Acquired for a research image collection, with no referral diagnosis; the patient describes having few moles overall; on a questionnaire the patient reported a personal history of skin cancer, a personal history of cancer, no family history of skin cancer, and no sunbed use: 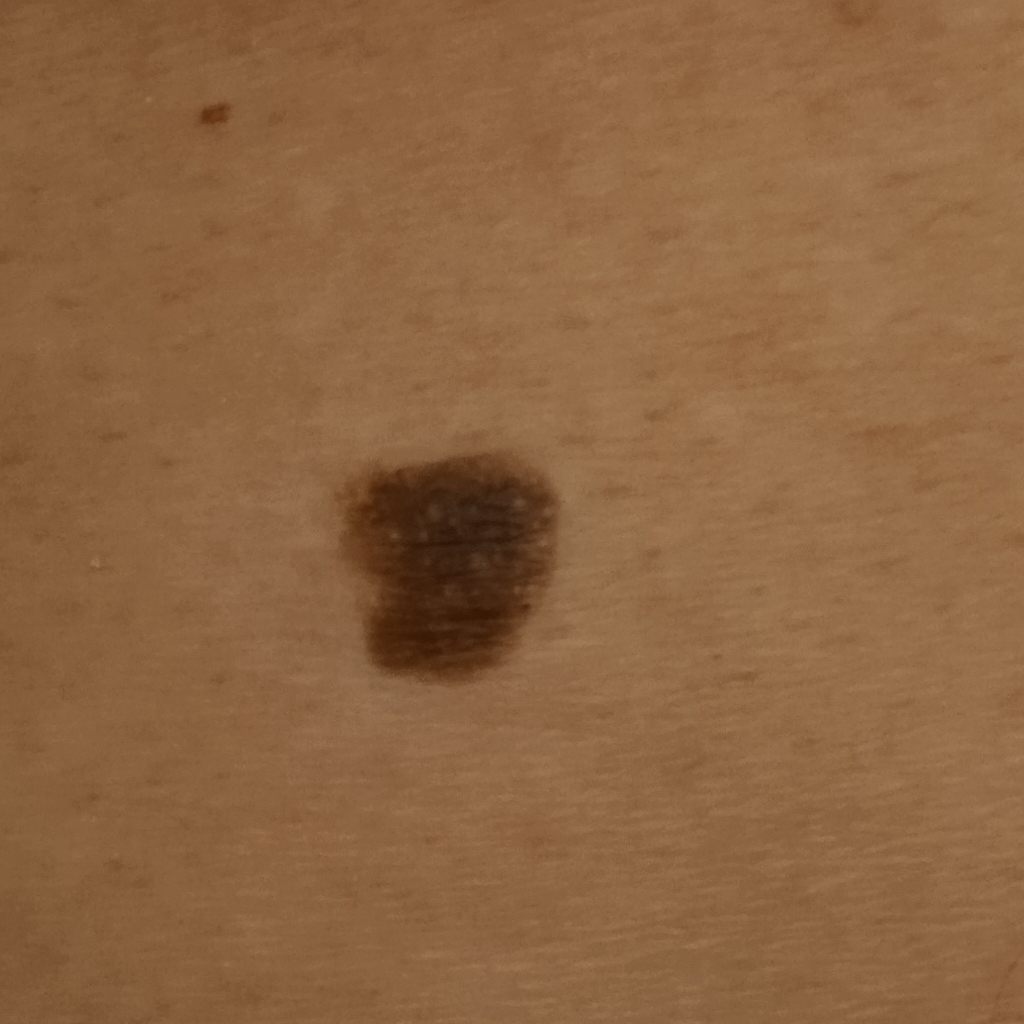The lesion is about 8.6 mm across.
The diagnostic impression was a seborrheic keratosis.